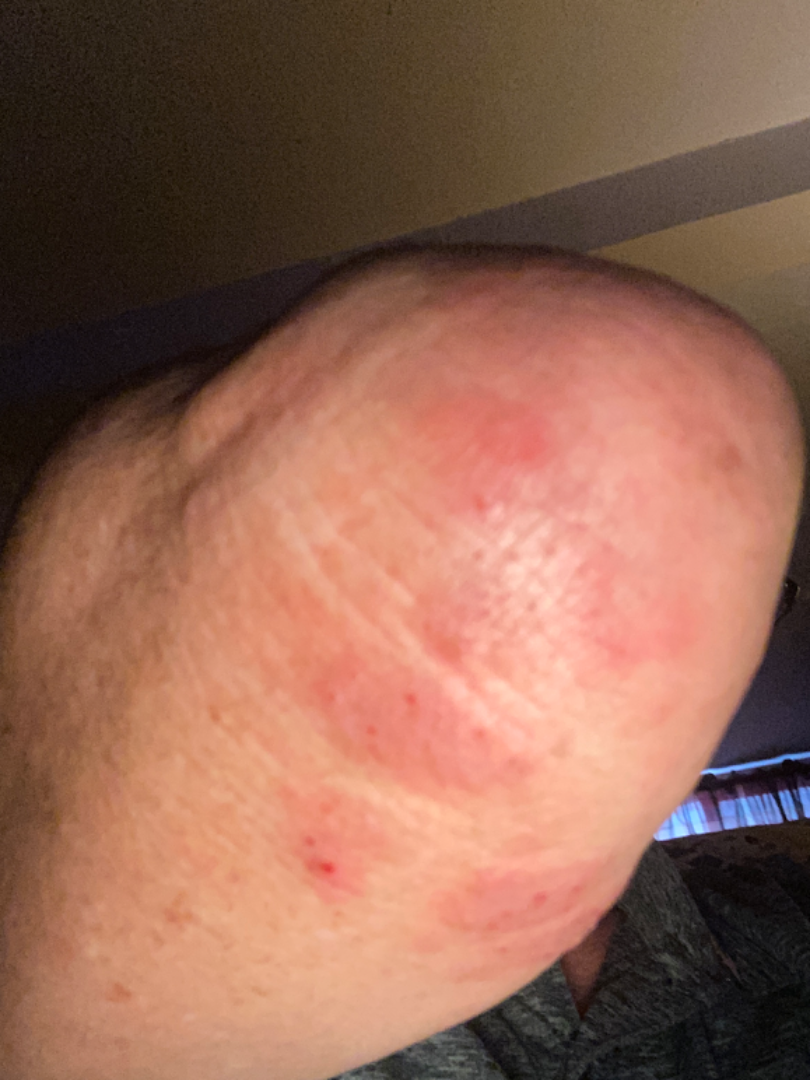The skin findings could not be characterized from the image. The patient considered this a rash. Present for more than one year. The photo was captured at an angle. Reported lesion symptoms include itching and burning. The patient reported no systemic symptoms.